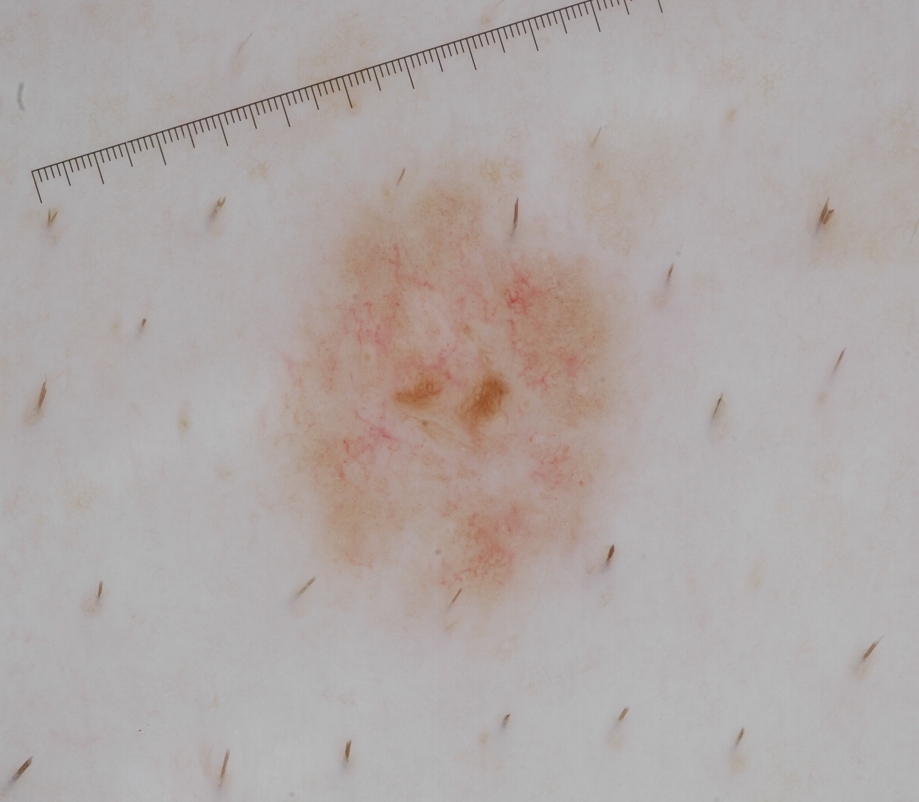Q: What is the imaging modality?
A: dermoscopic image
Q: Which assessed dermoscopic features were absent?
A: negative network, globules, pigment network, milia-like cysts, and streaks
Q: What is the lesion's bounding box?
A: [283, 157, 624, 613]
Q: How large is the lesion within the image?
A: ~15% of the field
Q: What is this lesion?
A: a melanocytic nevus